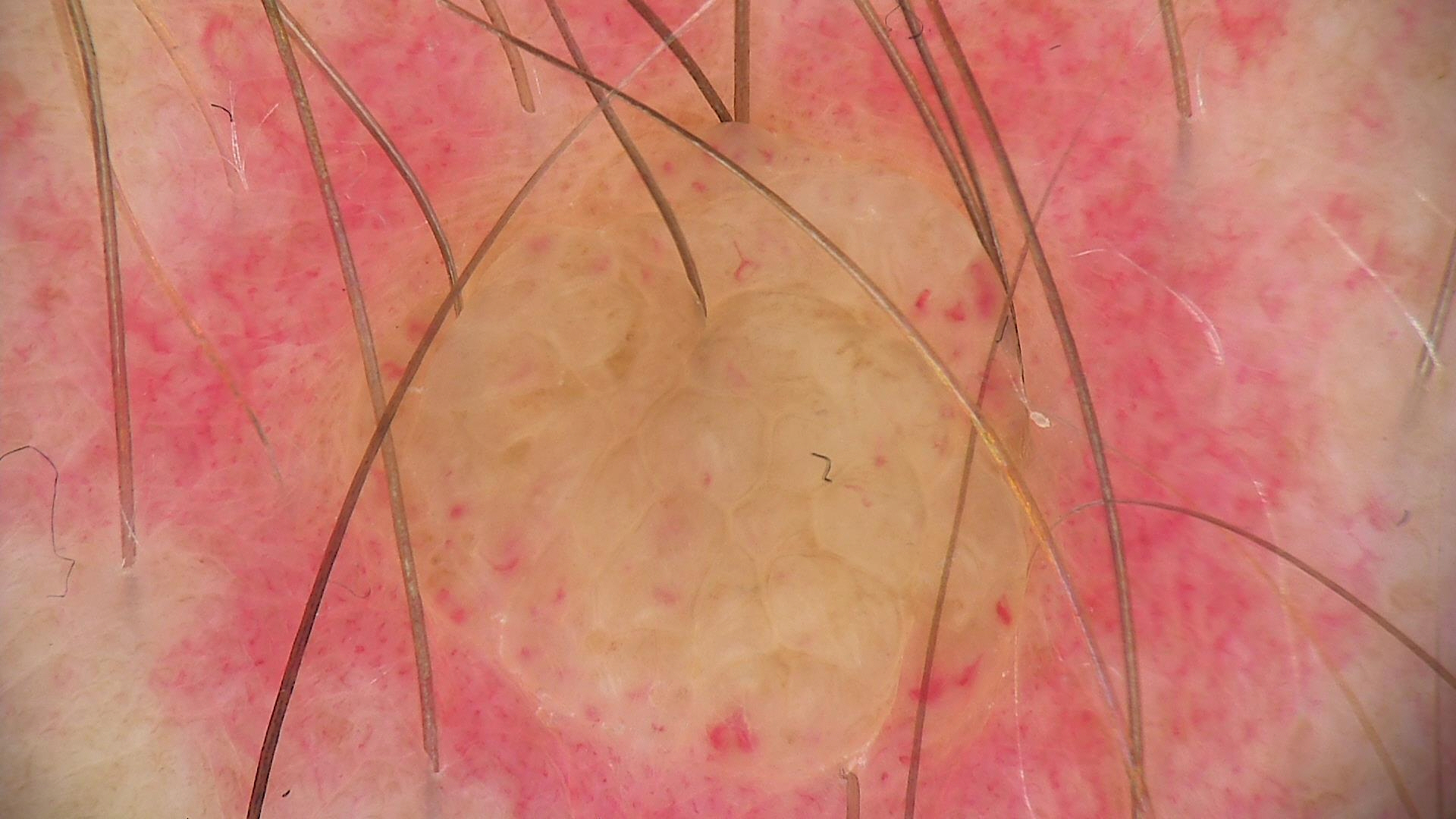category = banal | class = dermal nevus (expert consensus).